Female patient, age 18–29. This is a close-up image: 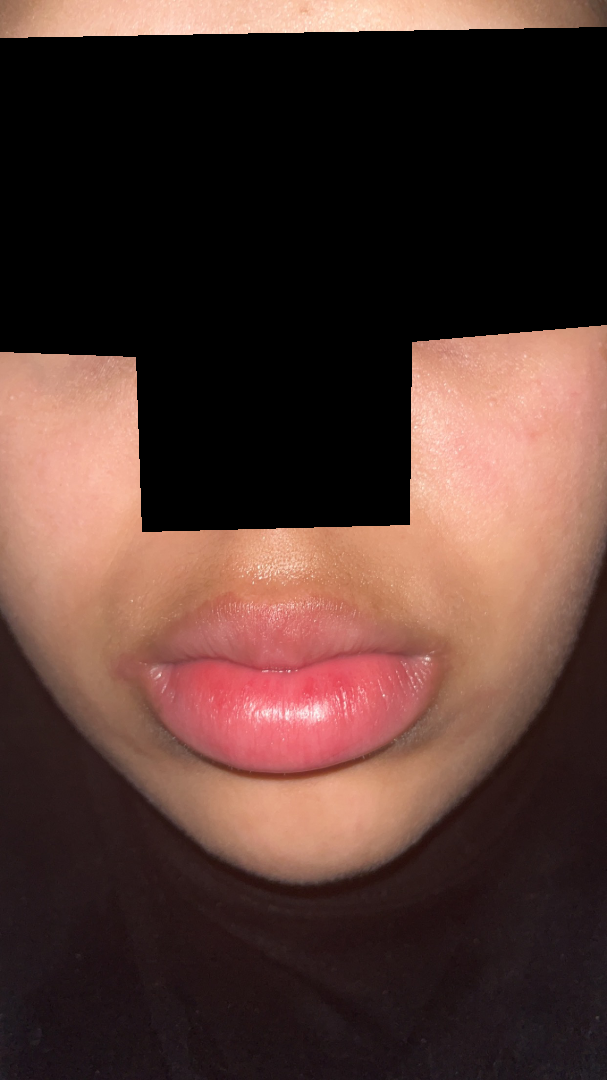<case>
<duration>three to twelve months</duration>
<texture>raised or bumpy, rough or flaky</texture>
<differential>
  <leading>Cheilitis</leading>
</differential>
</case>